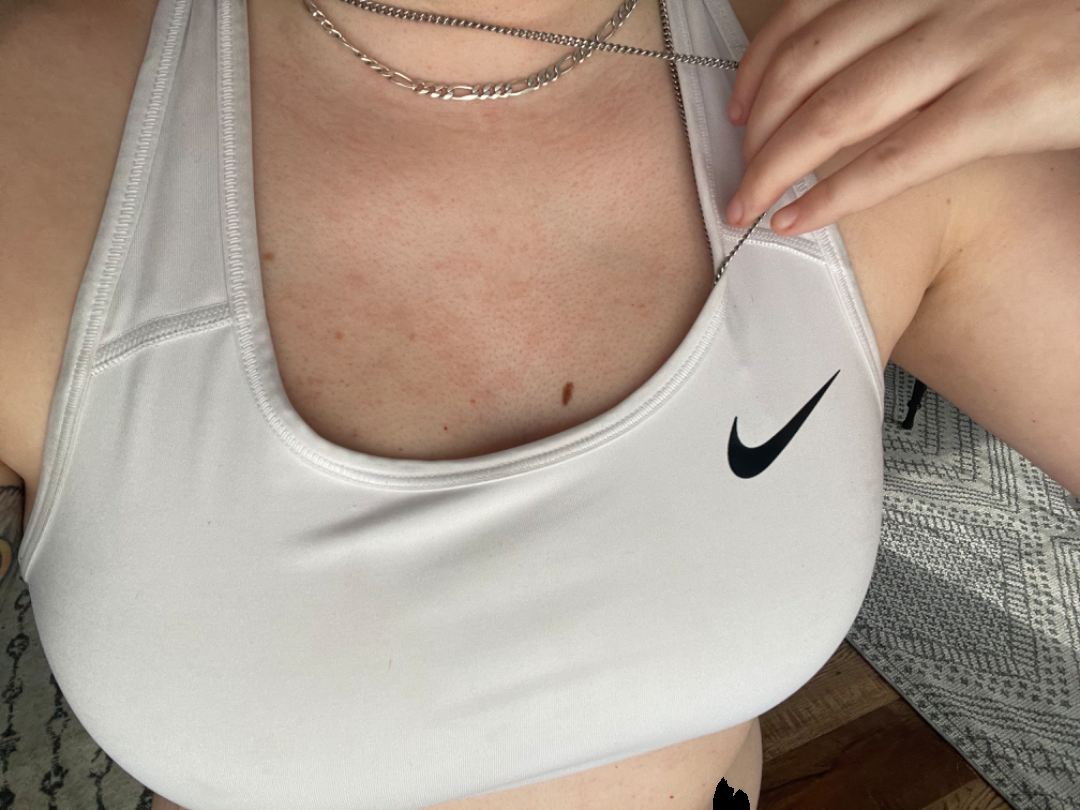The case was difficult to assess from the available photograph.
Reported duration is about one day.
The back of the torso, front of the torso and head or neck are involved.
No relevant lesion symptoms reported.
The patient indicates associated mouth sores.
A close-up photograph.
The patient indicates the lesion is raised or bumpy.